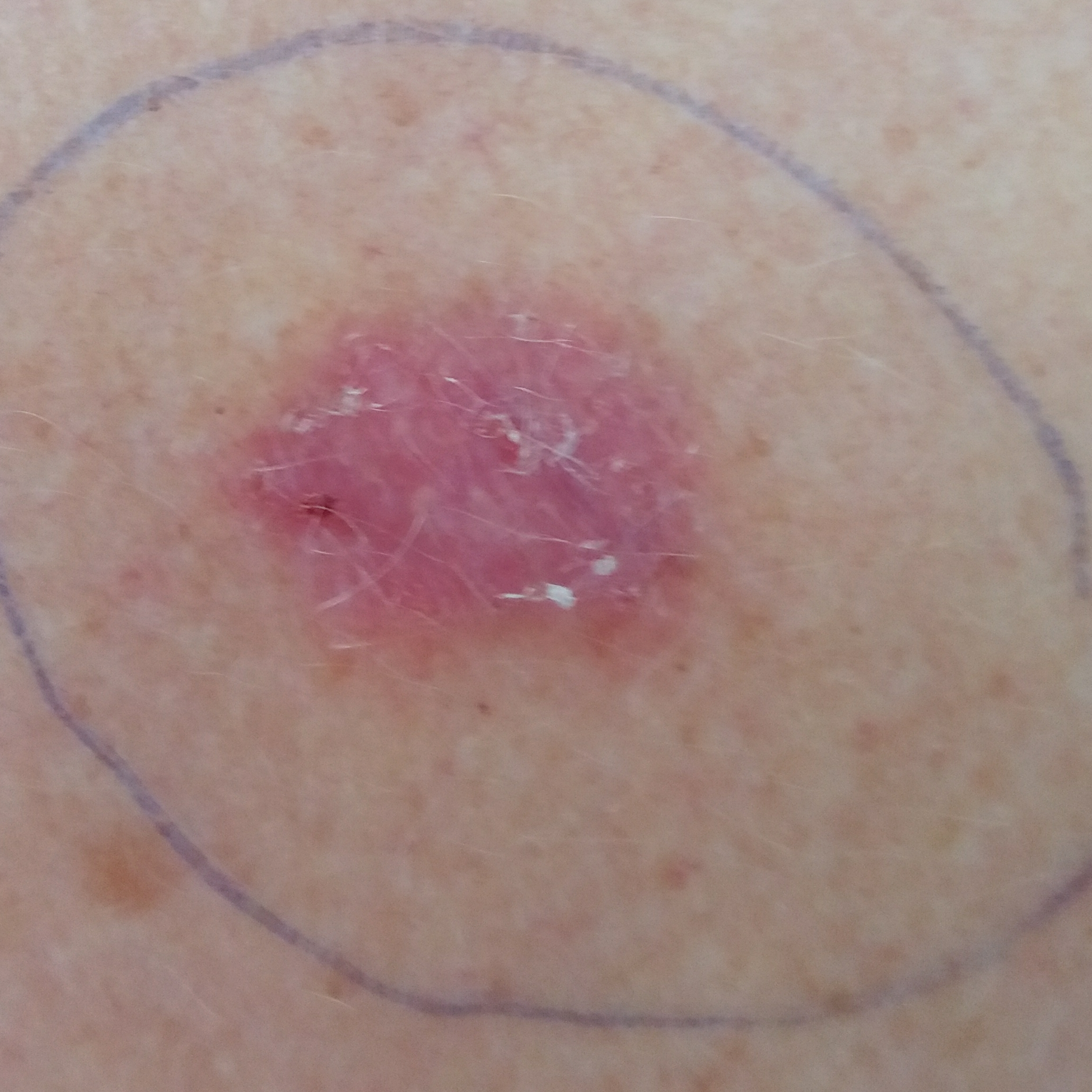Q: What are the relevant risk factors?
A: prior skin cancer (patient or family), prior malignancy (patient or family)
Q: What is the anatomic site?
A: the chest
Q: What symptoms does the patient report?
A: growth, change in appearance, itching
Q: What did the workup show?
A: basal cell carcinoma (biopsy-proven)